A dermatoscopic image of a skin lesion.
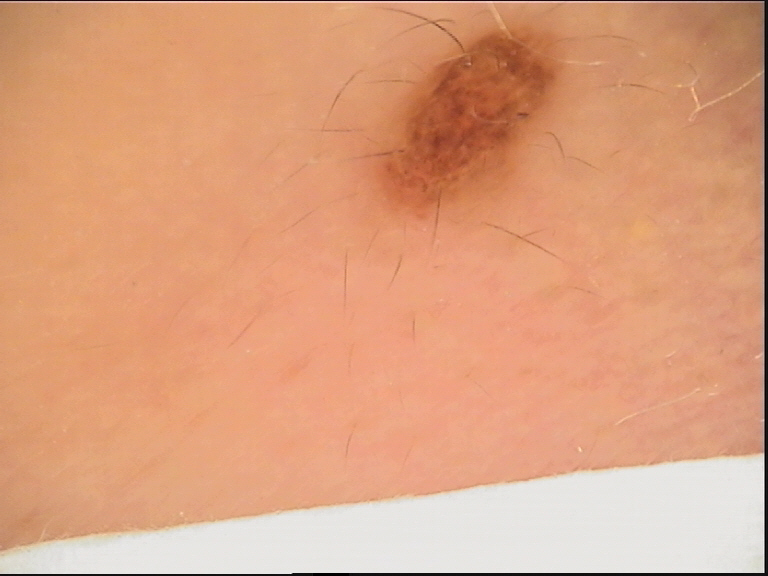assessment=dysplastic compound nevus (expert consensus).